An image taken at an angle. Reported lesion symptoms include itching. Located on the leg and arm. Male patient, age 40–49. Texture is reported as raised or bumpy. The patient described the issue as a rash:
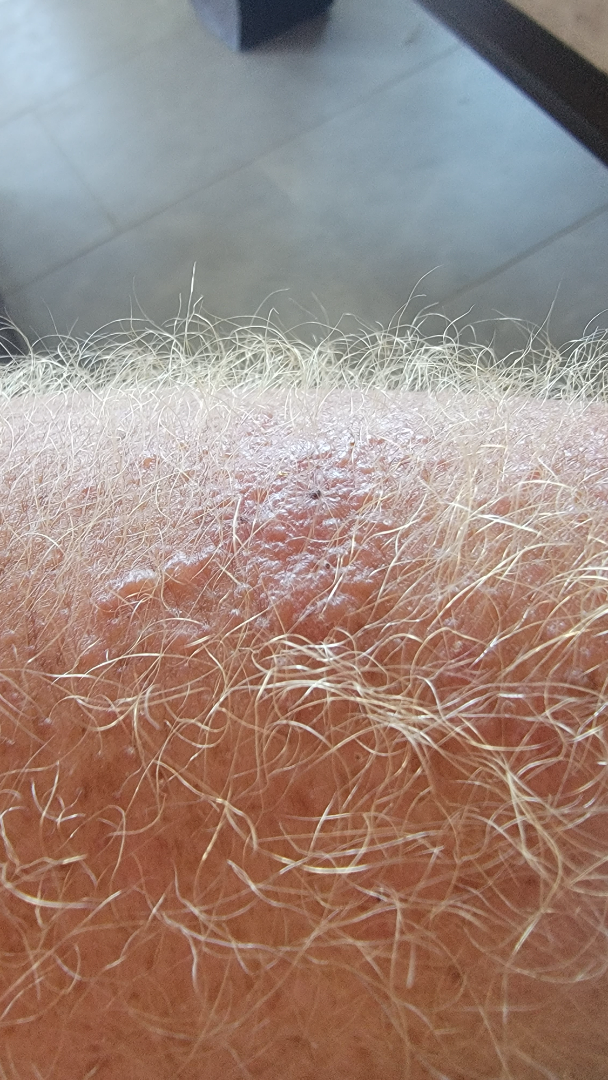assessment=unable to determine.